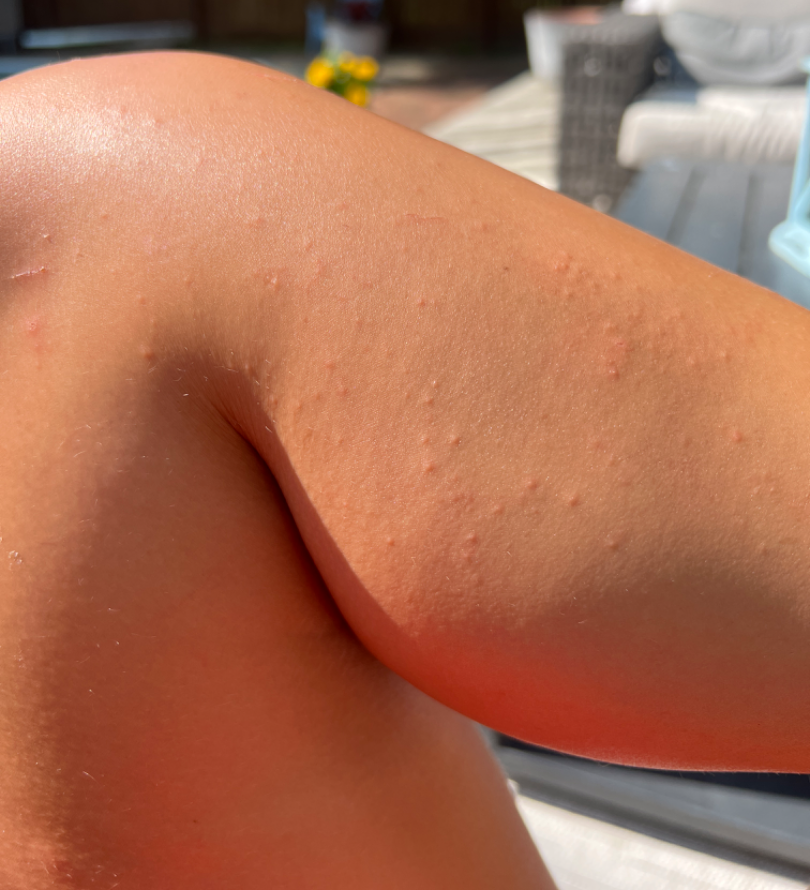This image was taken at an angle. The patient described the issue as a rash. The patient is a female aged 18–29. Texture is reported as raised or bumpy. Located on the leg and top or side of the foot. The patient reported no systemic symptoms. On dermatologist assessment of the image: in keeping with Folliculitis.